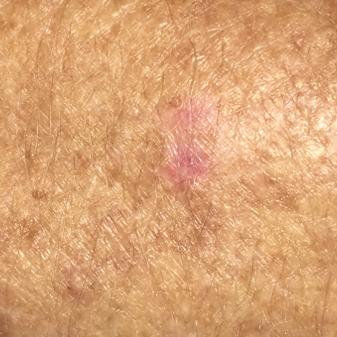Per patient report, the lesion itches. The diagnostic impression was a lesion with uncertain malignant potential — an actinic keratosis.